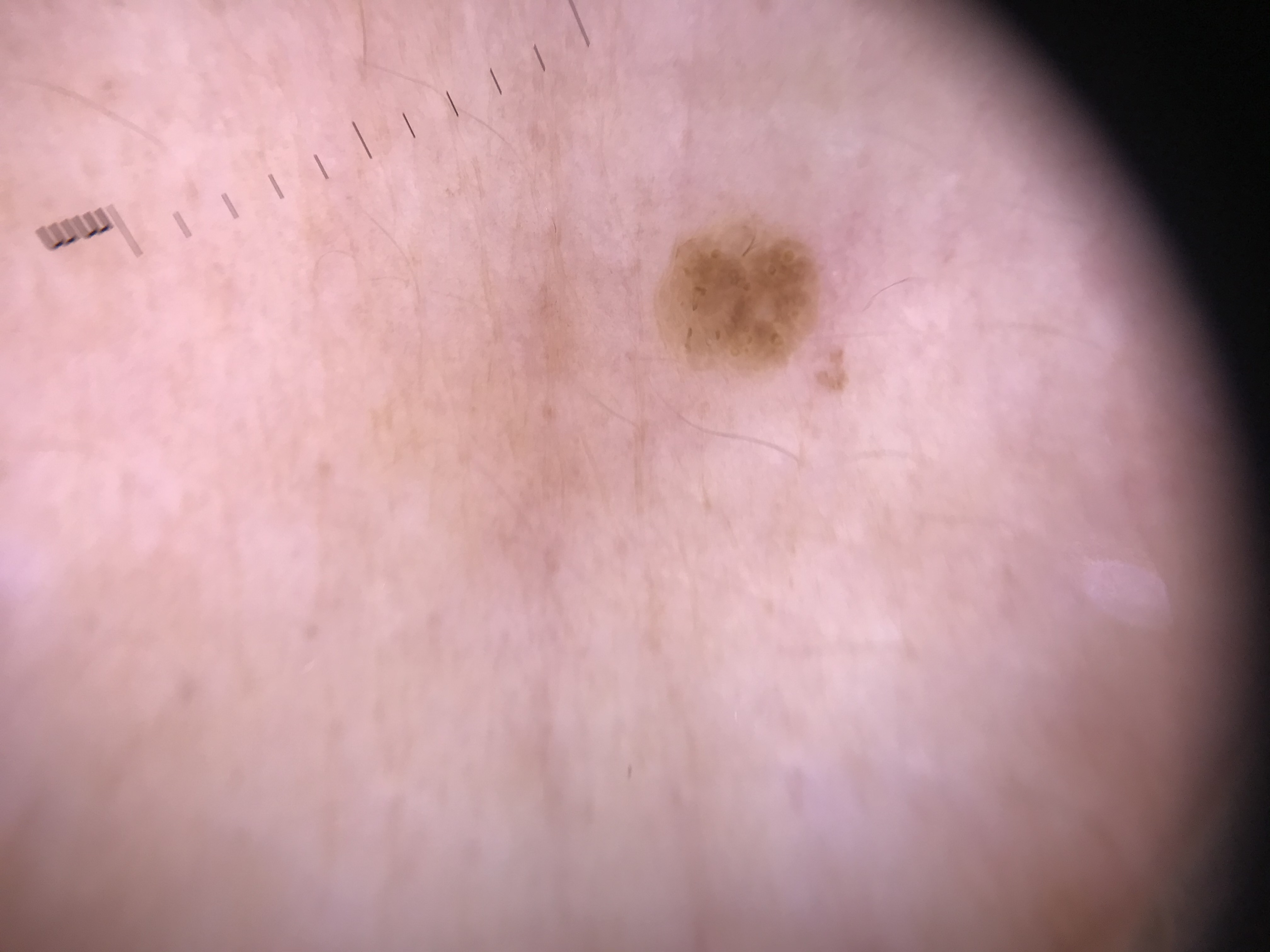A dermoscopic image of a skin lesion. The diagnosis was a keratinocytic lesion — a seborrheic keratosis.